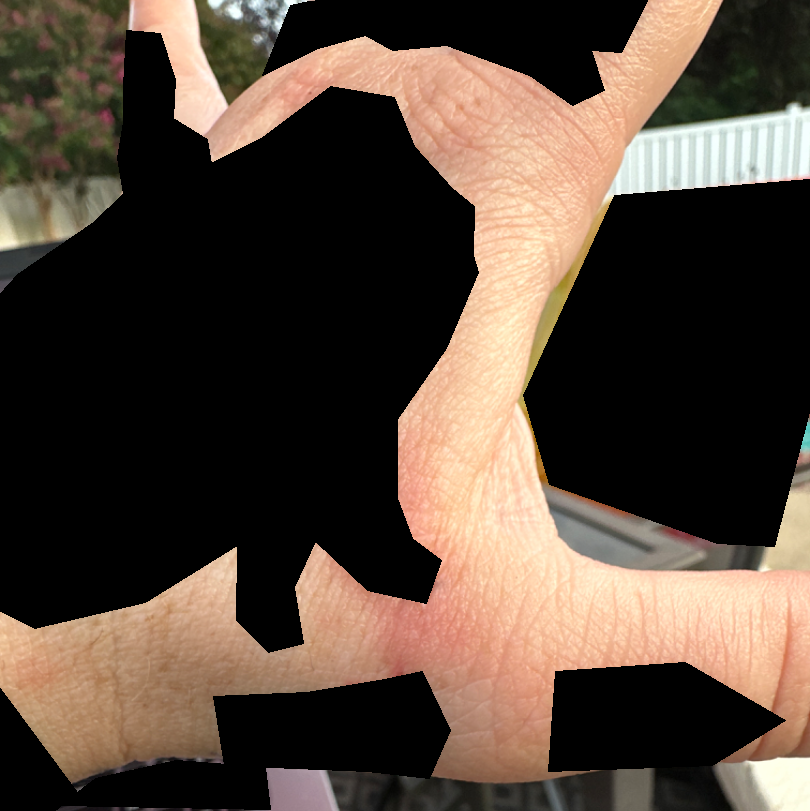assessment=most consistent with Eczema; an alternative is Allergic Contact Dermatitis; possibly Irritant Contact Dermatitis.